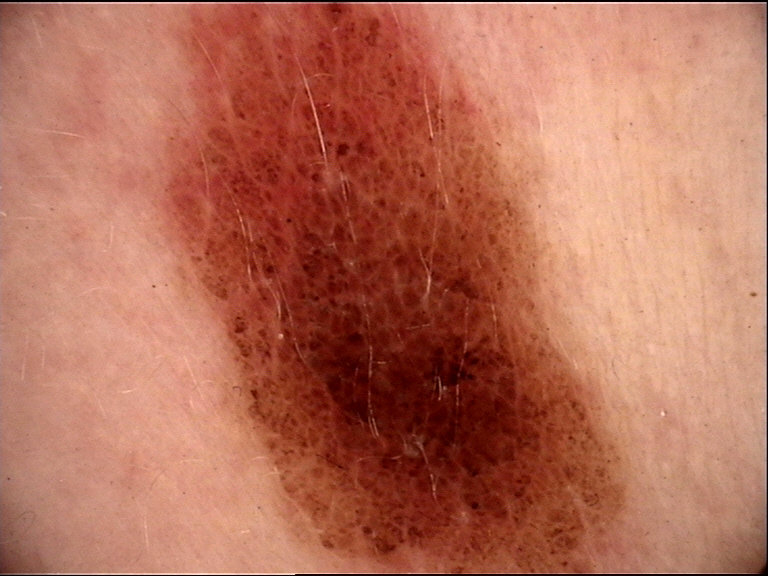A dermoscopic close-up of a skin lesion.
Consistent with a banal lesion — a compound nevus.